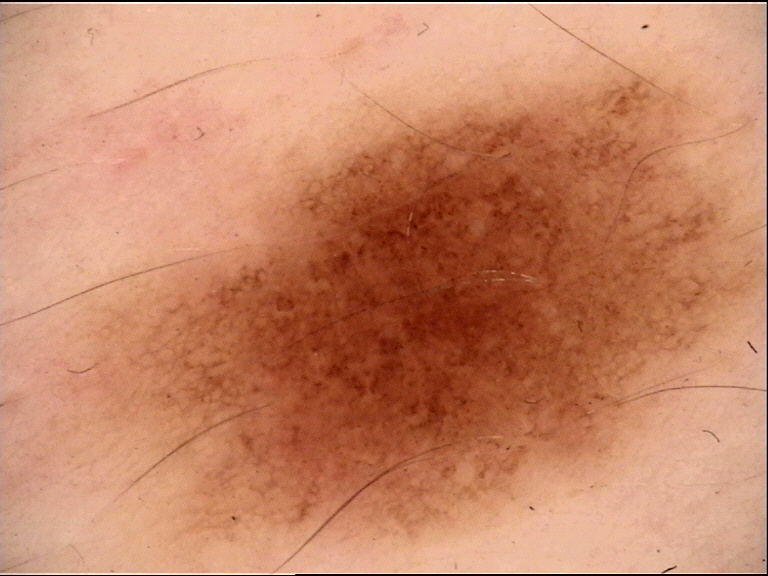Findings:
- image type: dermoscopy
- class: dysplastic junctional nevus (expert consensus)